The photo was captured at an angle. The affected area is the front of the torso — 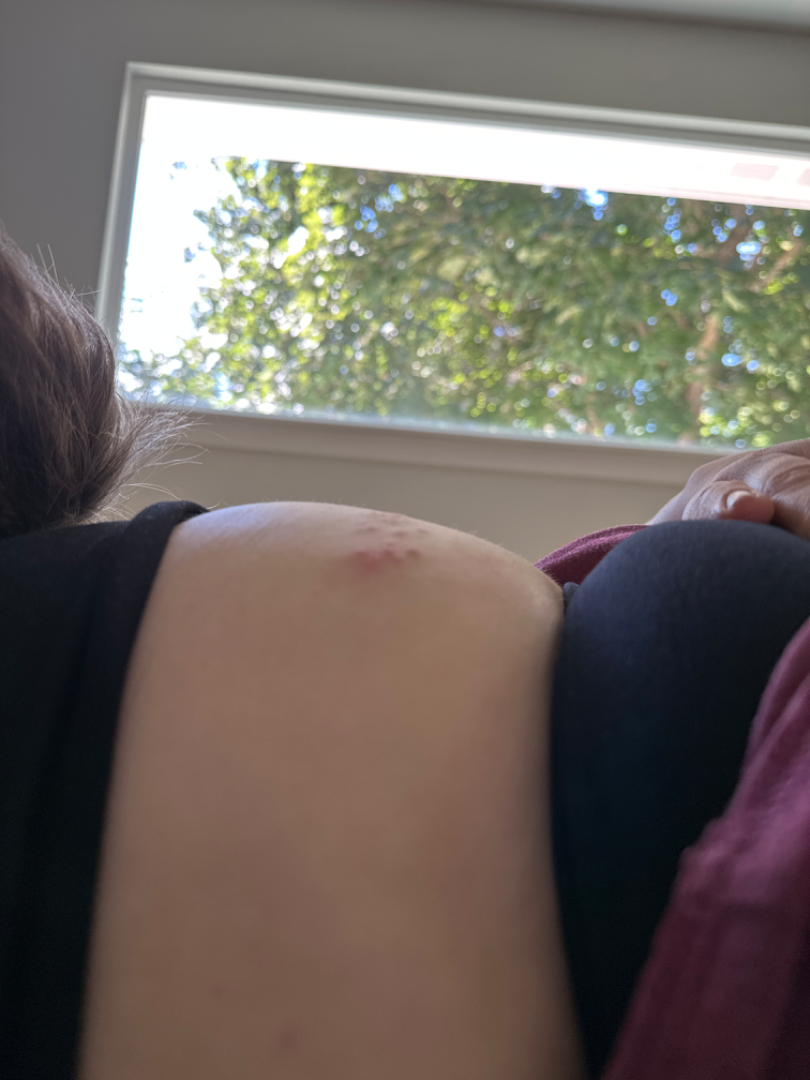Assessment: On remote review of the image, Herpes Simplex (leading); Herpes Zoster (possible); Skin and soft tissue atypical mycobacterial infection (less likely).